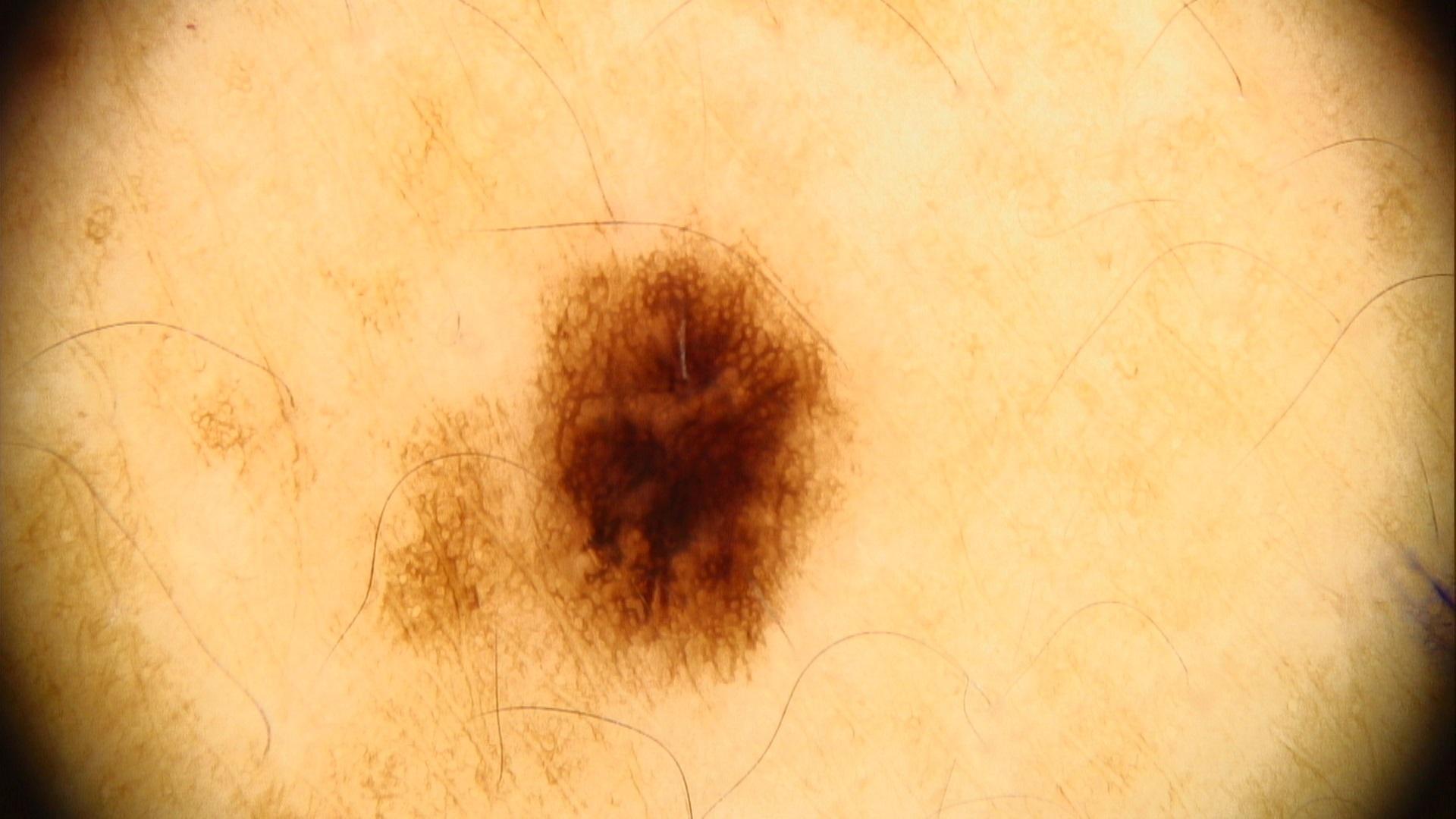Expert review favored a nevus.